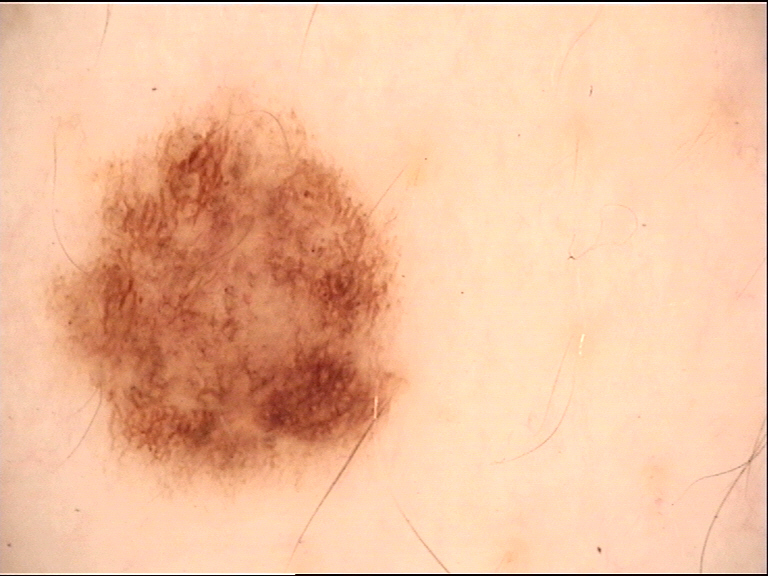Diagnosed as a dysplastic junctional nevus.